The photograph is a close-up of the affected area:
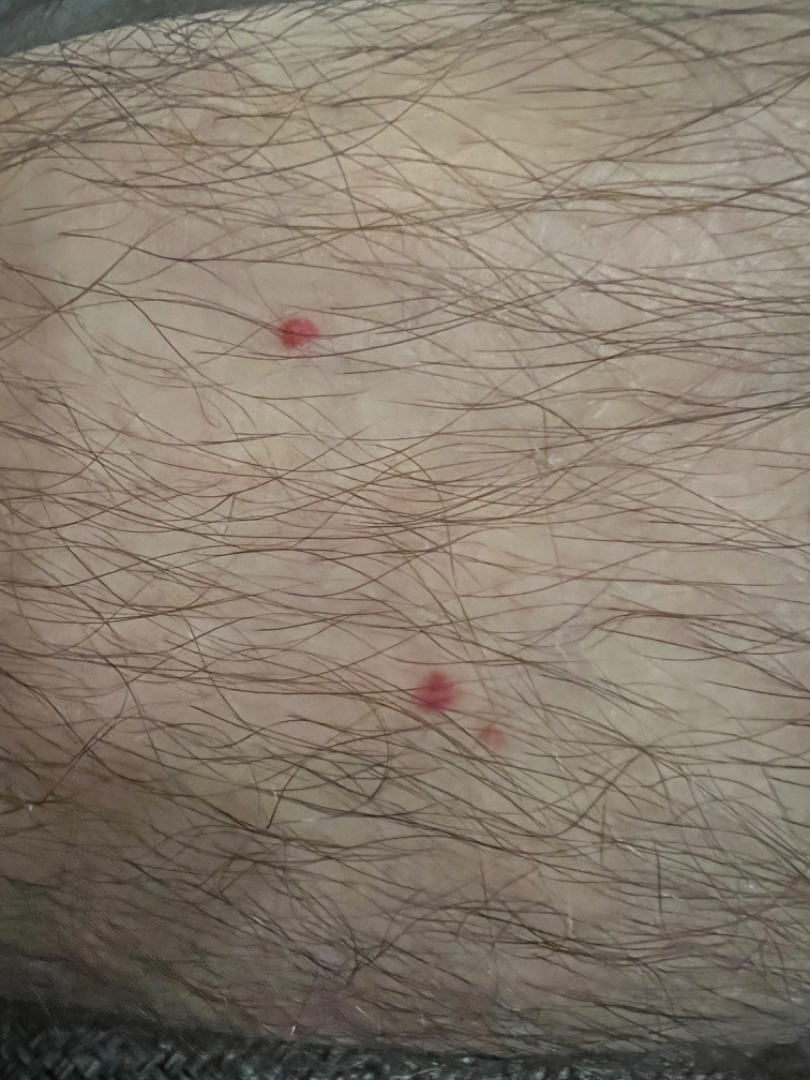assessment = indeterminate.